The chart notes prior skin cancer (patient or family), pesticide exposure, alcohol use, prior malignancy (patient or family), and no tobacco use. A male subject 43 years of age. Fitzpatrick III:
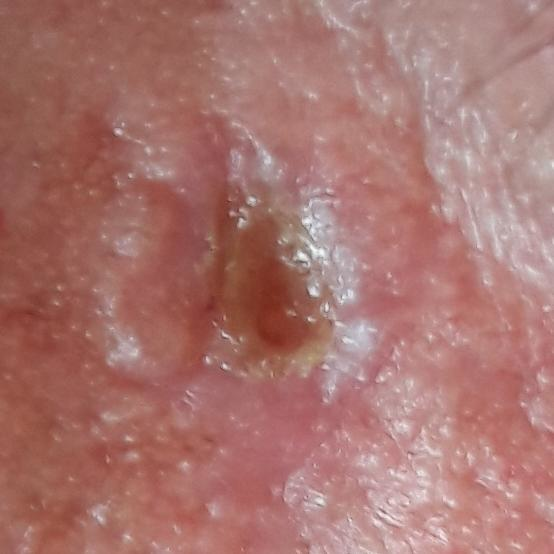Summary: The lesion is located on the face. The lesion measures approximately 4 × 4 mm. Conclusion: On biopsy, the diagnosis was a squamous cell carcinoma.